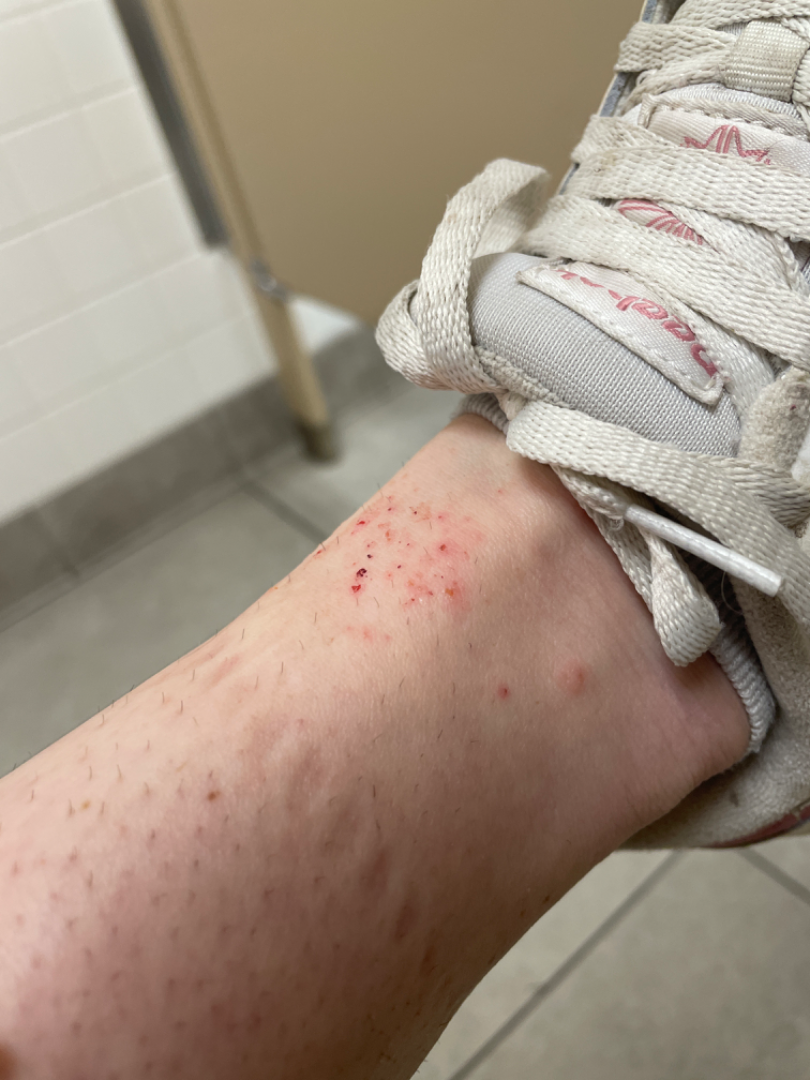surface texture: raised or bumpy
symptoms: burning, enlargement and itching
patient describes the issue as: a rash
photo taken: at an angle
anatomic site: back of the hand, leg and top or side of the foot
other reported symptoms: none reported
onset: less than one week
impression: the favored diagnosis is Superficial wound of body region; the differential also includes Inflicted skin lesions; a remote consideration is Irritant Contact Dermatitis